Symptoms reported: itching; this image was taken at an angle; self-categorized by the patient as a rash; located on the head or neck; reported duration is about one day; the lesion is described as raised or bumpy: 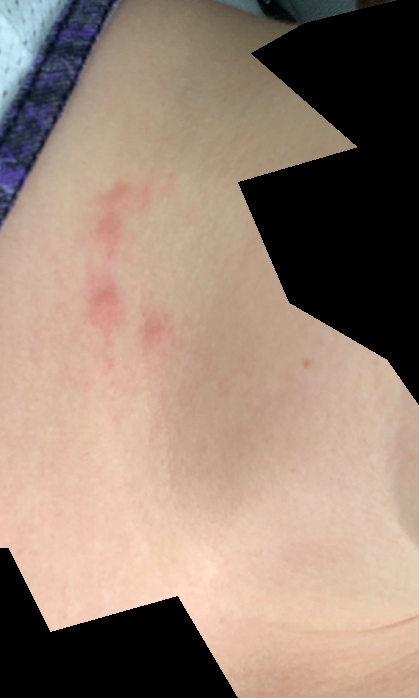Findings: The case was difficult to assess from the available photograph.